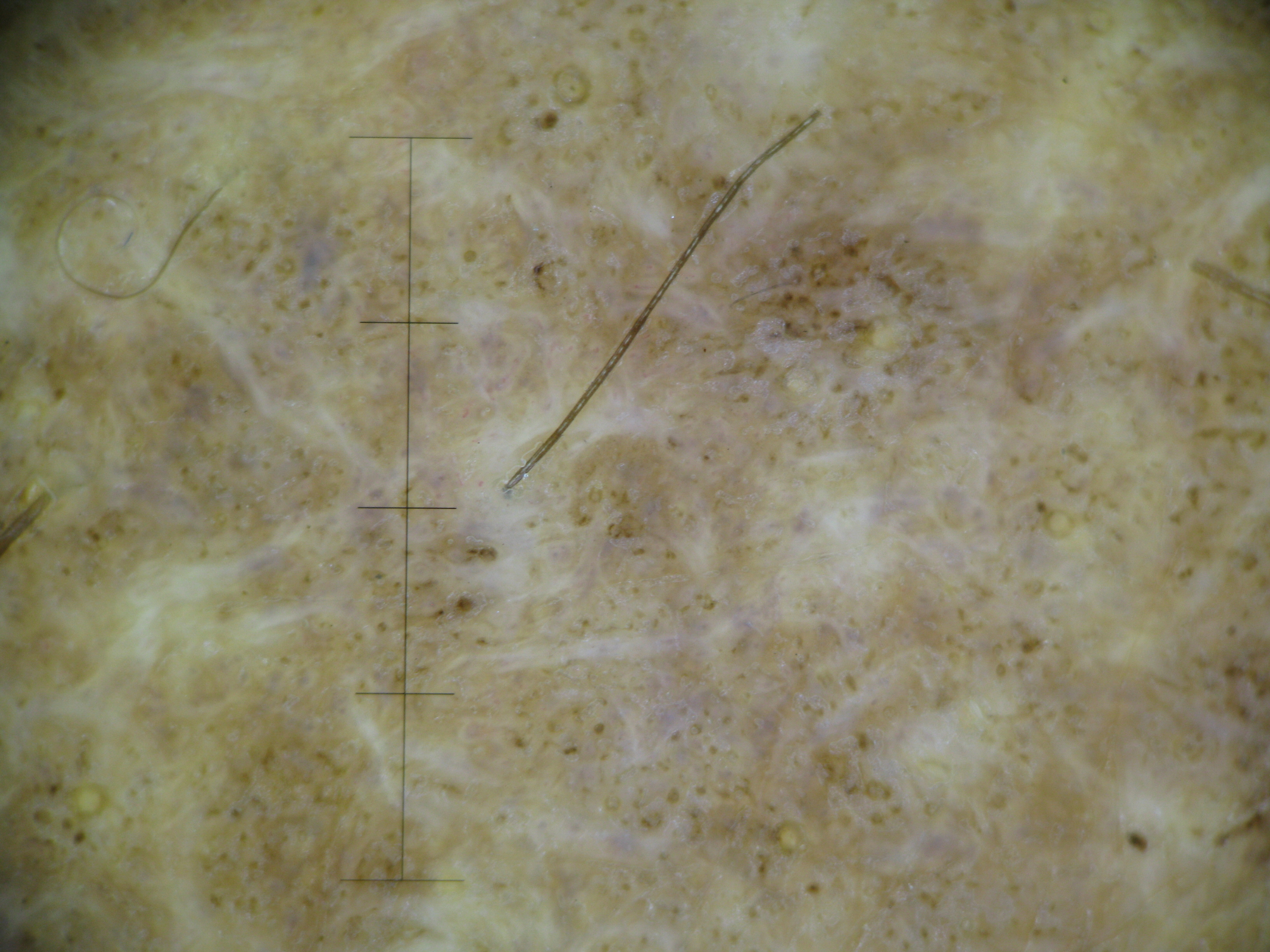classification=banal | label=congenital compound nevus (expert consensus).